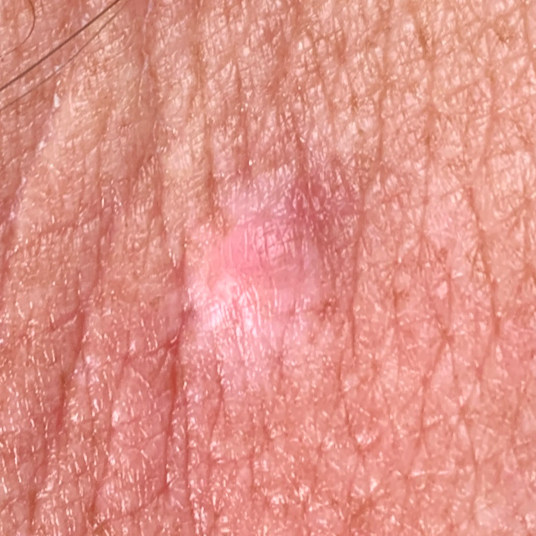imaging = smartphone clinical photo | FST = III | subject = female, age 53 | reported symptoms = elevation | pathology = basal cell carcinoma (biopsy-proven).